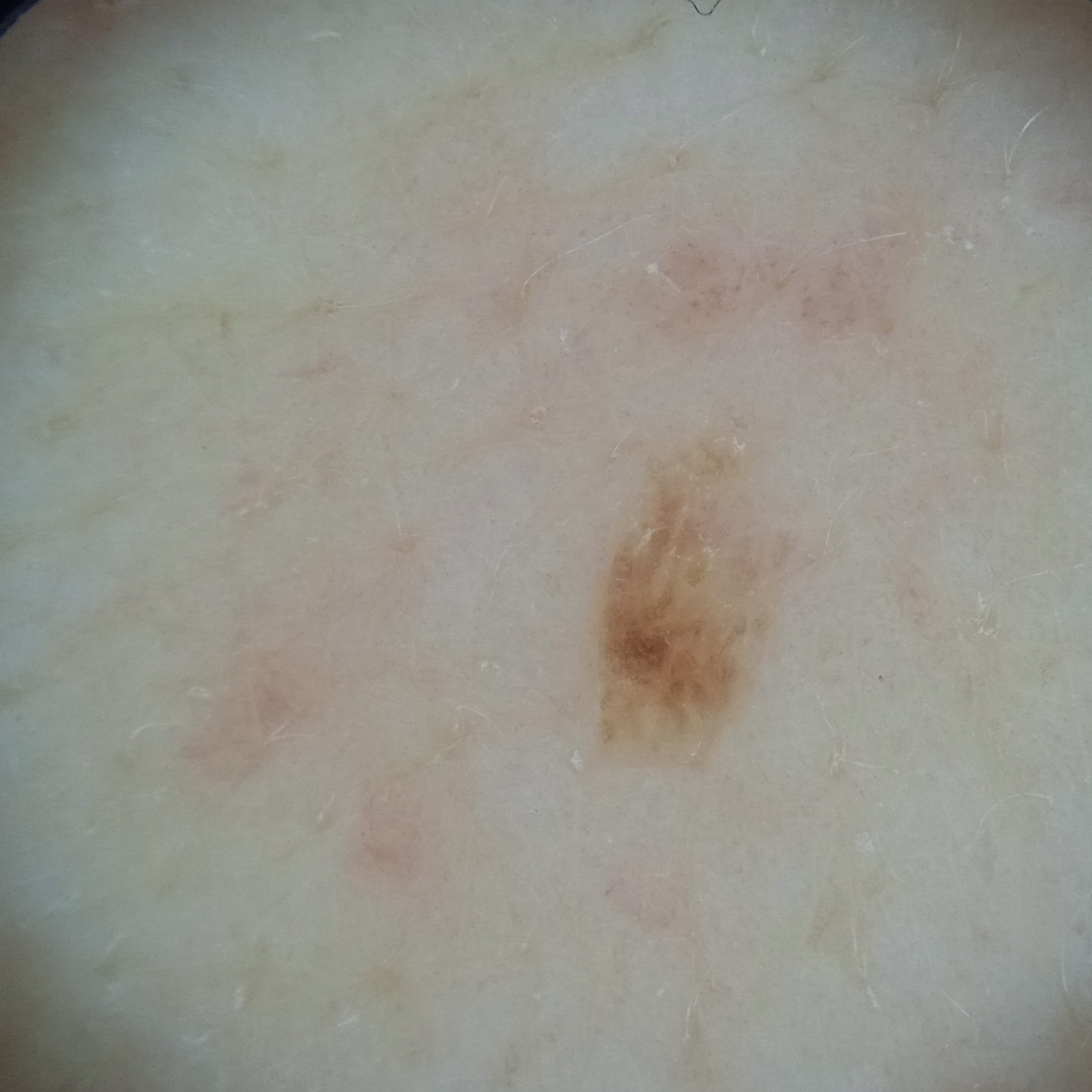Findings:
- sun reaction · skin reddens with sun exposure
- referral · research study (no referral diagnosis)
- patient · female, 71 years of age
- nevus count · few melanocytic nevi overall
- risk factors · a personal history of skin cancer, a personal history of cancer, no sunbed use, no family history of skin cancer
- imaging · dermoscopy
- location · the back
- diameter · 3.8 mm
- diagnosis · seborrheic keratosis (dermatologist consensus)